Self-categorized by the patient as a nail problem, the photo was captured at an angle, texture is reported as raised or bumpy, symptoms reported: bothersome appearance, present for one to three months, the subject is a female aged 50–59, no constitutional symptoms were reported, Fitzpatrick phototype III — 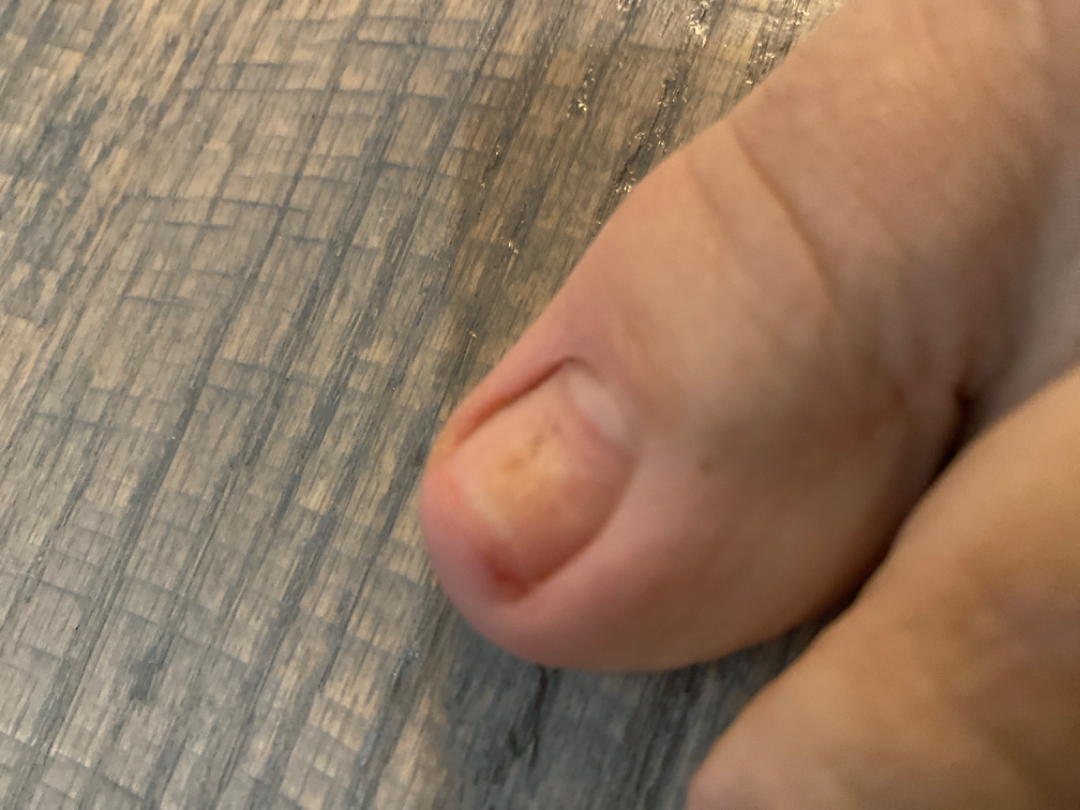Q: What is the dermatologist's impression?
A: the favored diagnosis is Onychodystrophy; also consider Onychomycosis